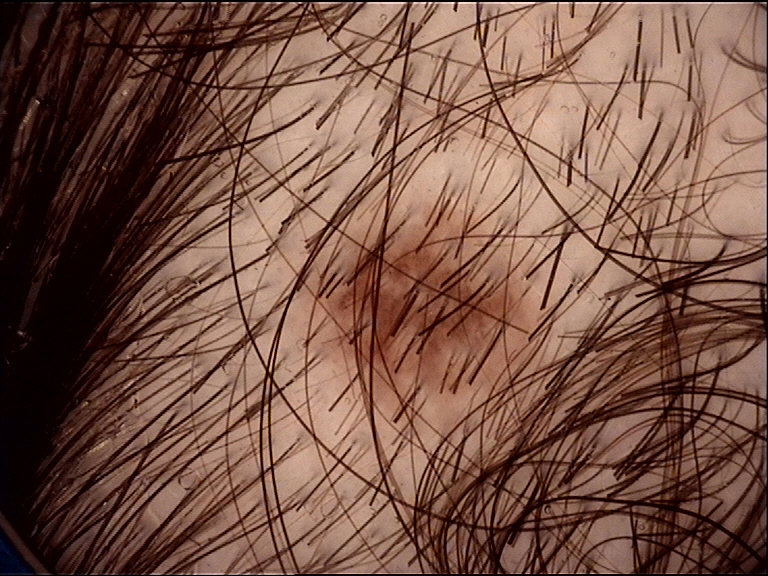Q: What kind of image is this?
A: dermoscopy
Q: What is the diagnosis?
A: dysplastic junctional nevus (expert consensus)